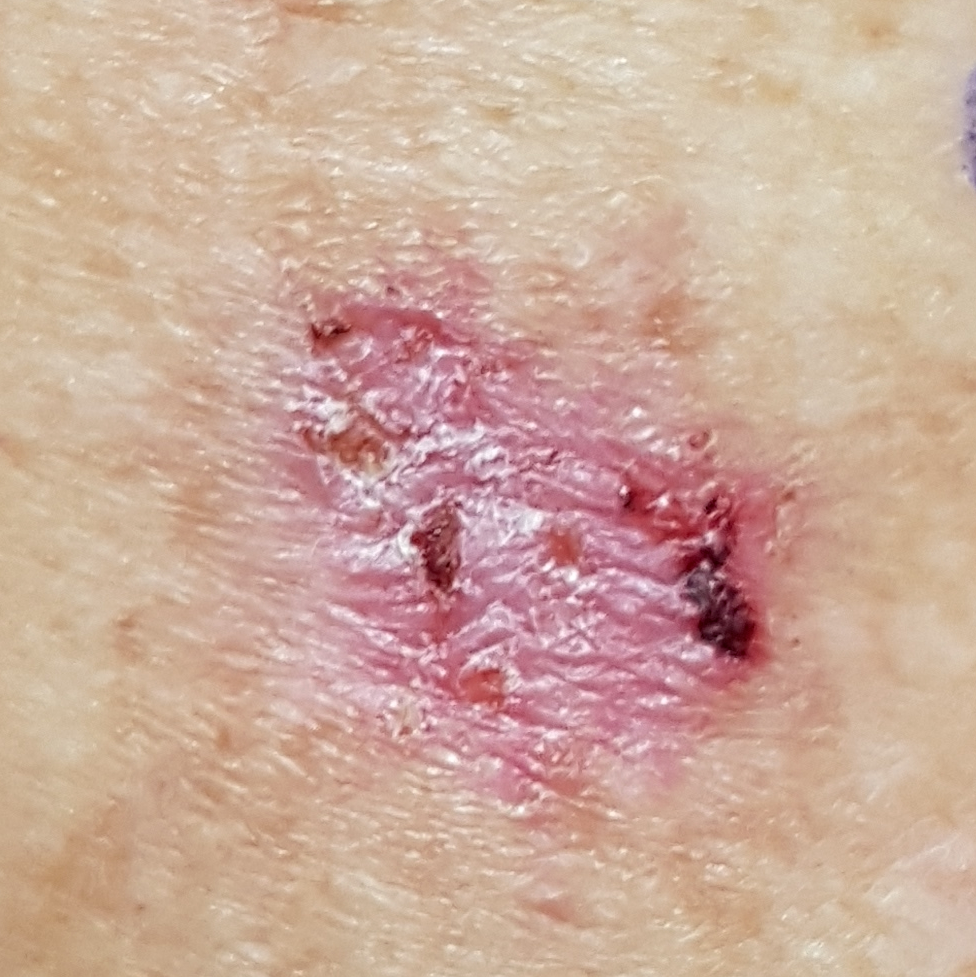Summary: A female subject 56 years of age. Fitzpatrick phototype I. The chart notes prior skin cancer (patient or family). A clinical photograph of a skin lesion. The lesion was found on an arm. Conclusion: On biopsy, the diagnosis was a malignant skin lesion — a basal cell carcinoma.